The back of the torso is involved. The lesion is associated with enlargement, itching and darkening. A close-up photograph. Self-categorized by the patient as a rash. Reported duration is less than one week. The lesion is described as raised or bumpy:
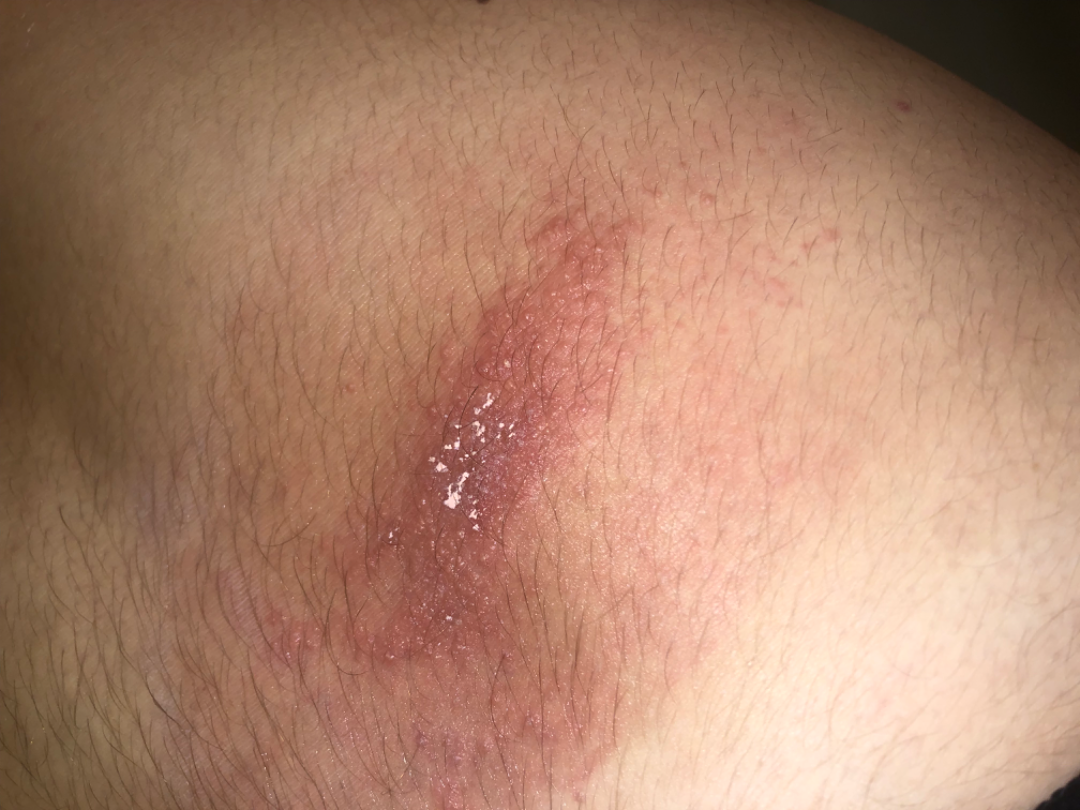assessment: unable to determine